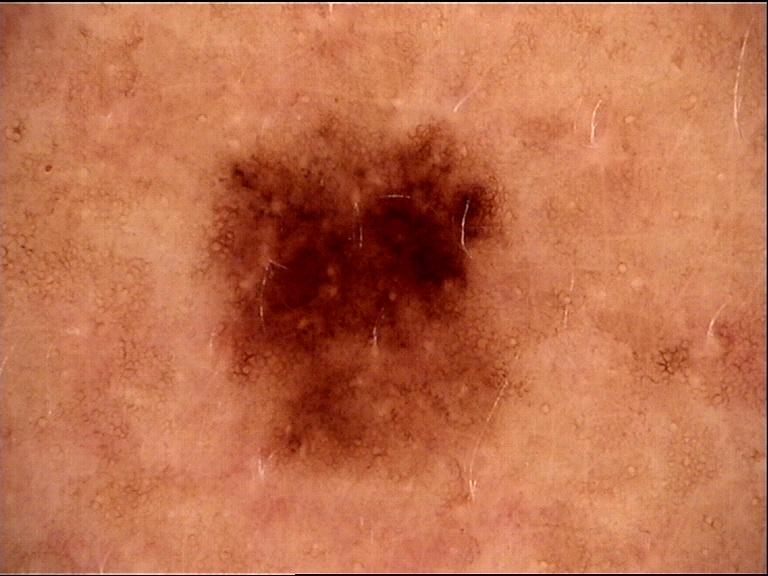imaging=dermatoscopy; assessment=dysplastic junctional nevus (expert consensus).